The subject is a female aged 13 to 17 · a dermatoscopic image of a skin lesion — 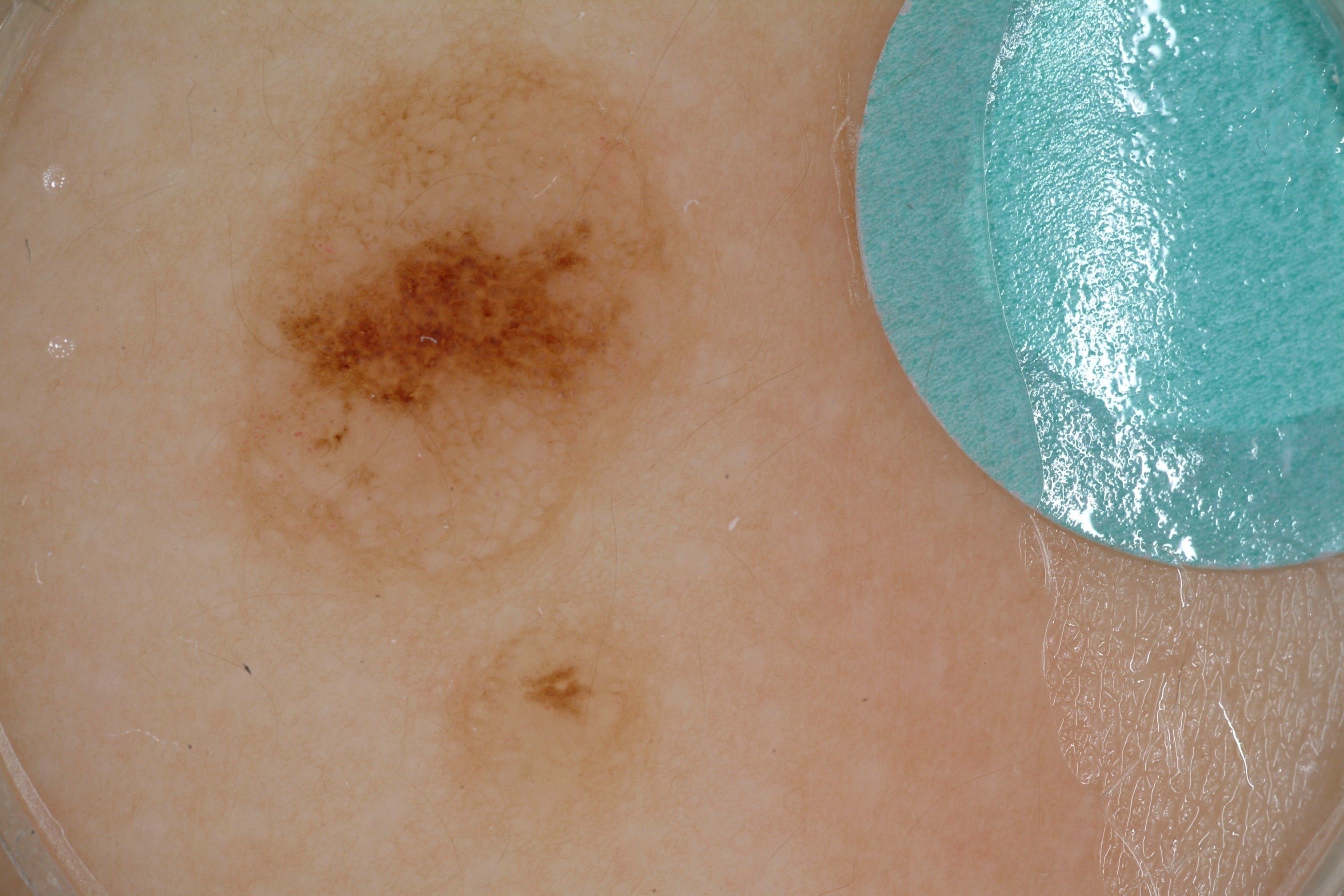In (x1, y1, x2, y2) order, the lesion occupies the region [218, 13, 707, 613]. Dermoscopy demonstrates pigment network and globules. The diagnostic assessment was a melanocytic nevus.